This is a close-up image:
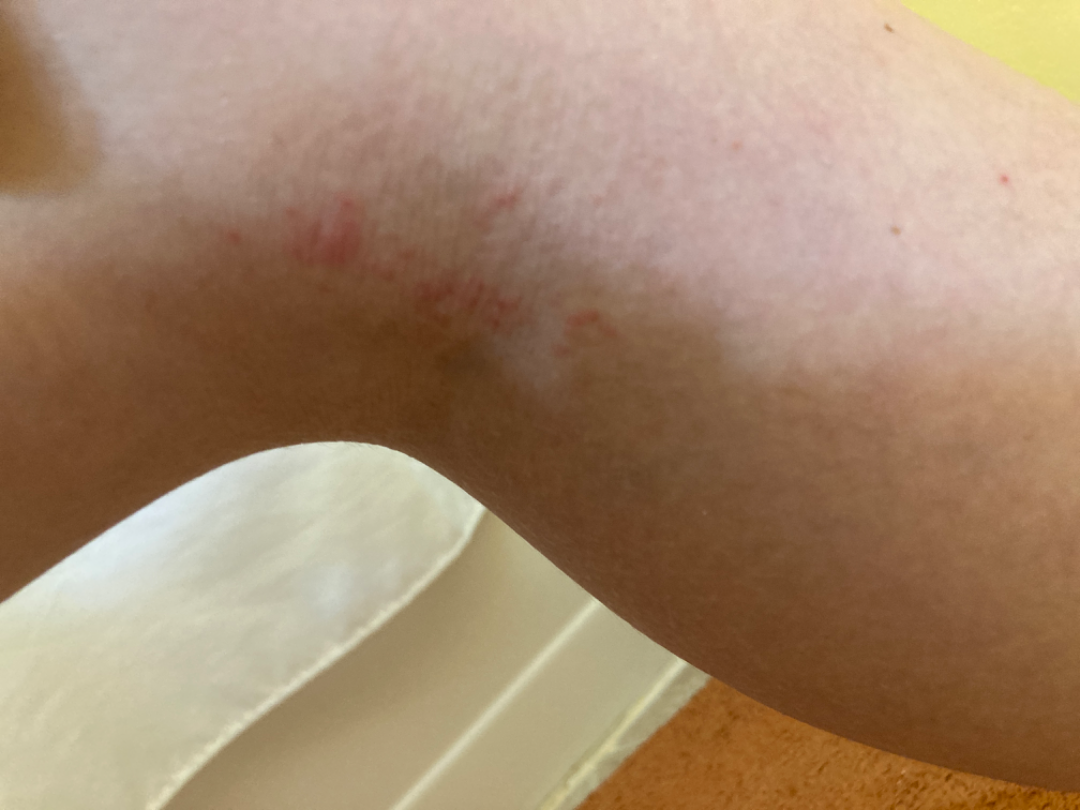Q: What conditions are considered?
A: Eczema and Allergic Contact Dermatitis were considered with similar weight